Close-up view · the patient described the issue as a rash · reported lesion symptoms include itching · the lesion is described as raised or bumpy · the condition has been present for less than one week — 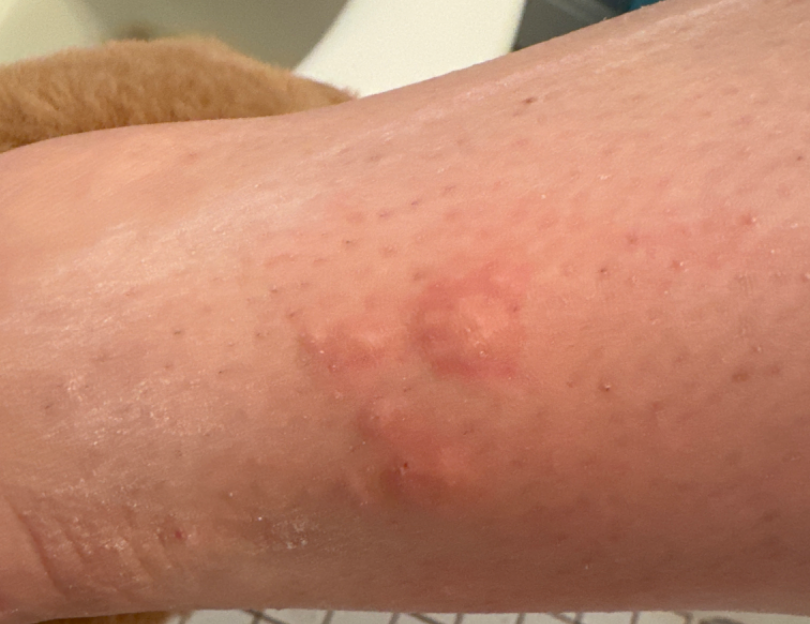Findings: The reviewing clinician's impression was: favoring Insect Bite.